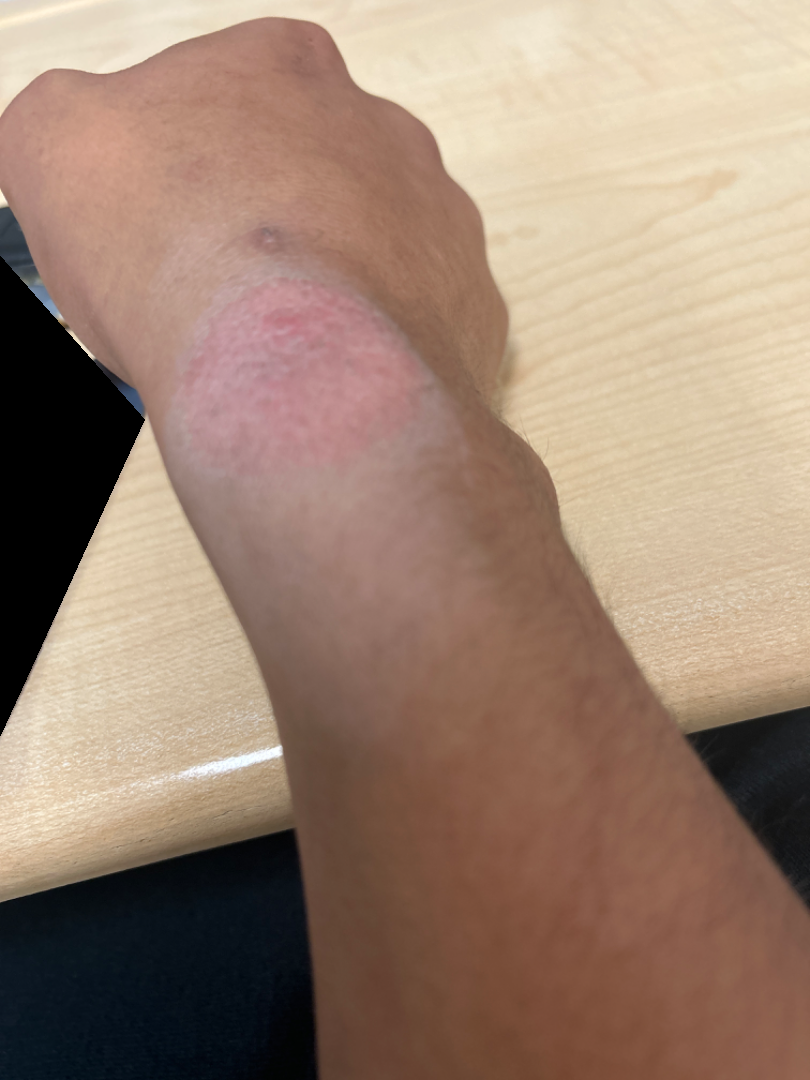Review: Single-reviewer assessment: favoring Allergic Contact Dermatitis; also raised was Irritant Contact Dermatitis.